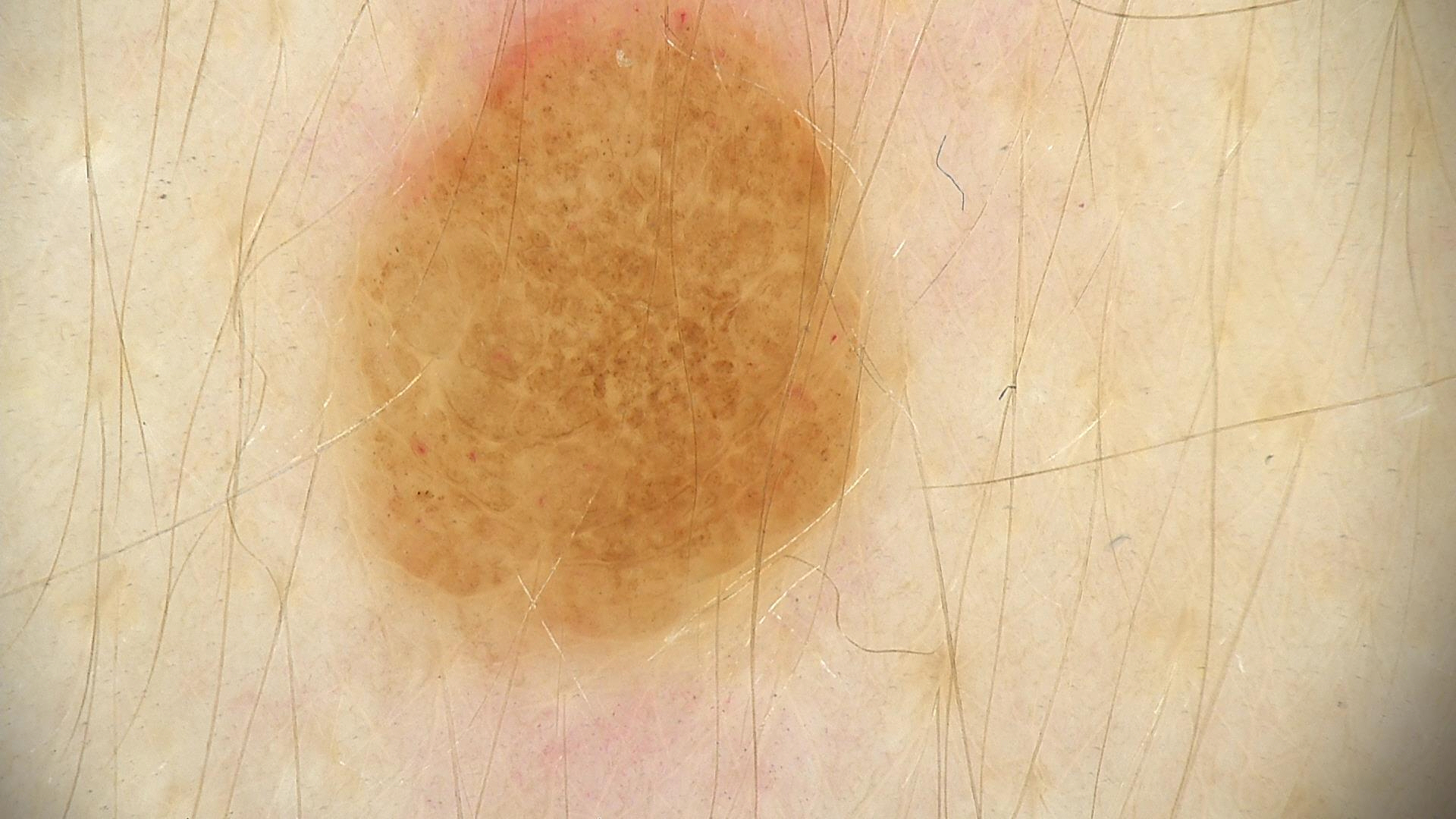modality = dermoscopy
assessment = compound nevus (expert consensus)